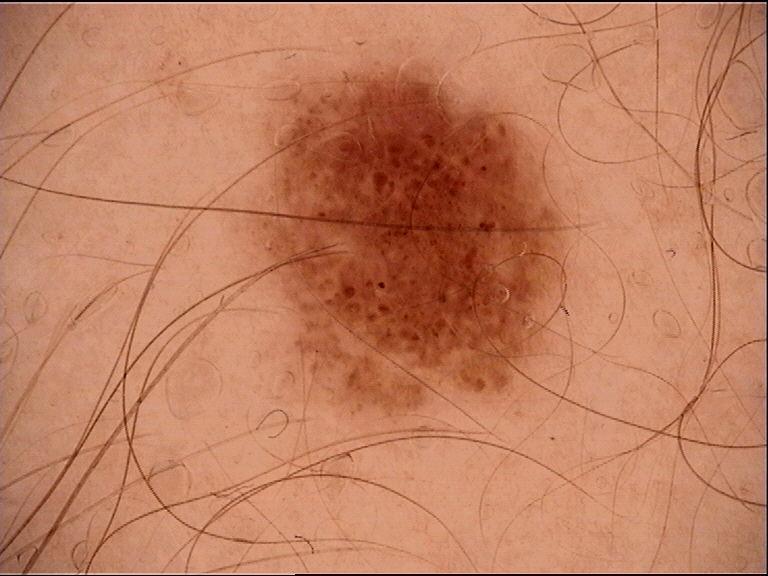Labeled as a dysplastic junctional nevus.